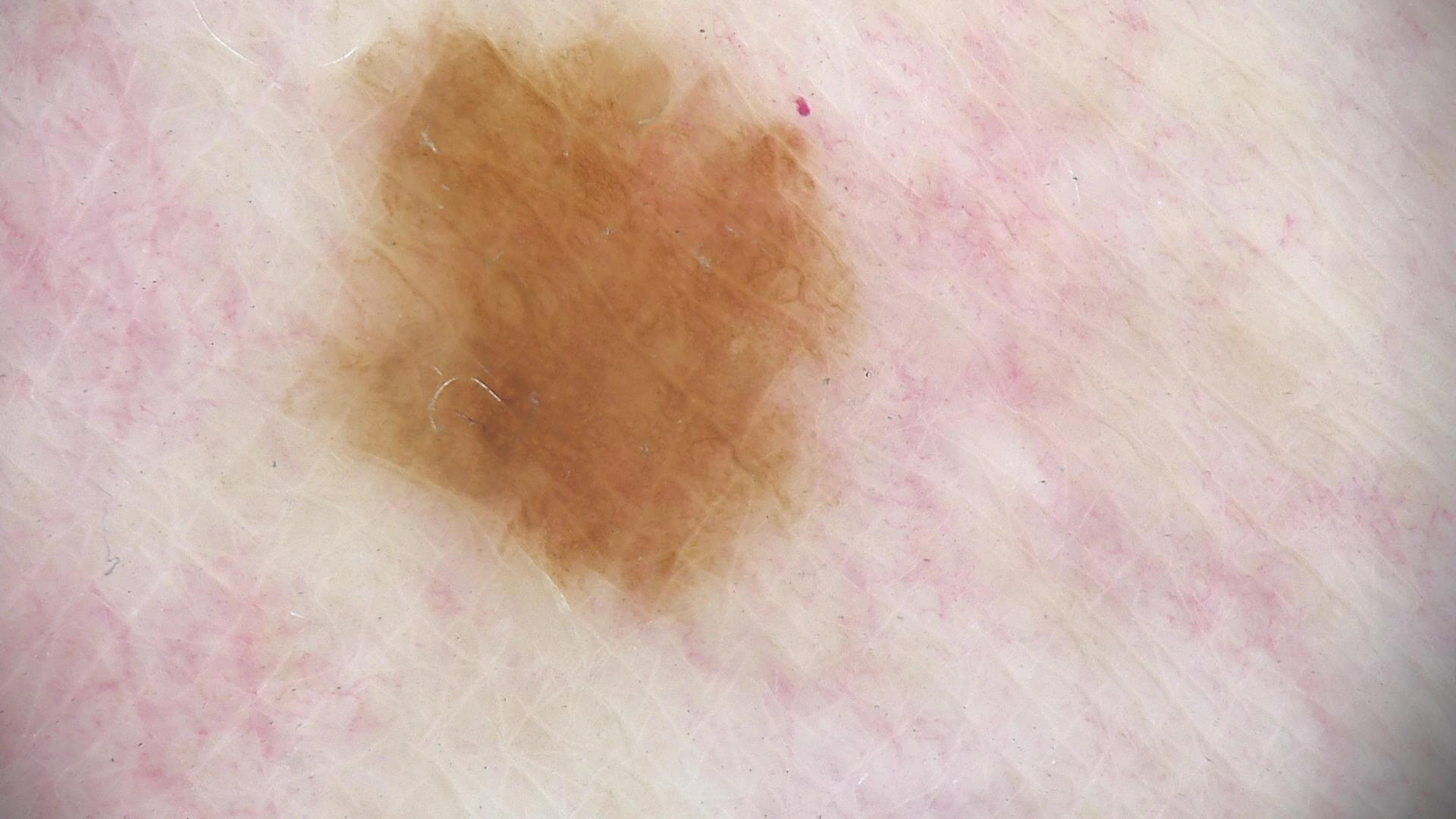Impression:
Classified as a dysplastic junctional nevus.